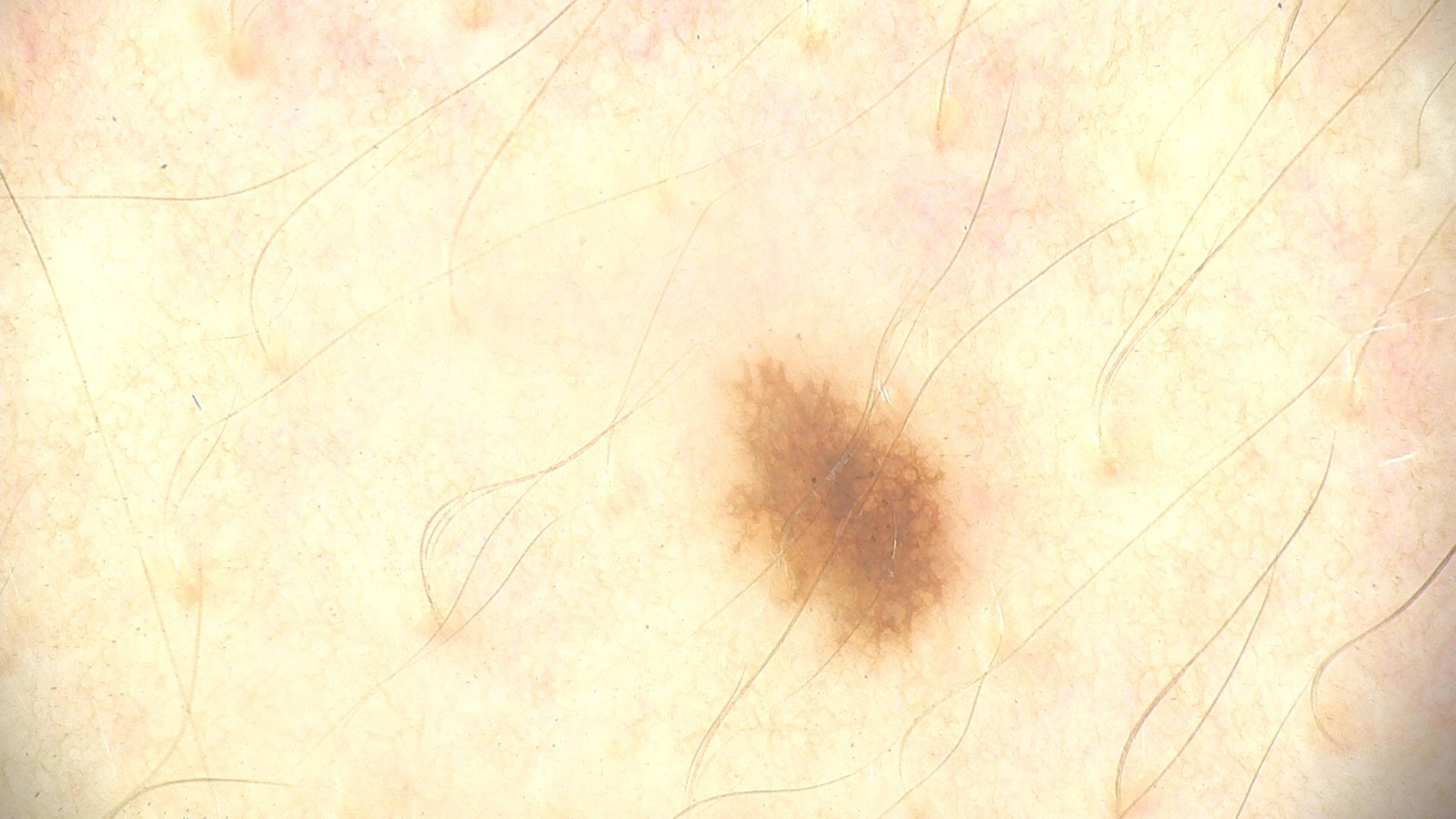Diagnosed as a dysplastic junctional nevus.